A clinical photo of a skin lesion taken with a smartphone · skin type V · a female patient in their 50s: 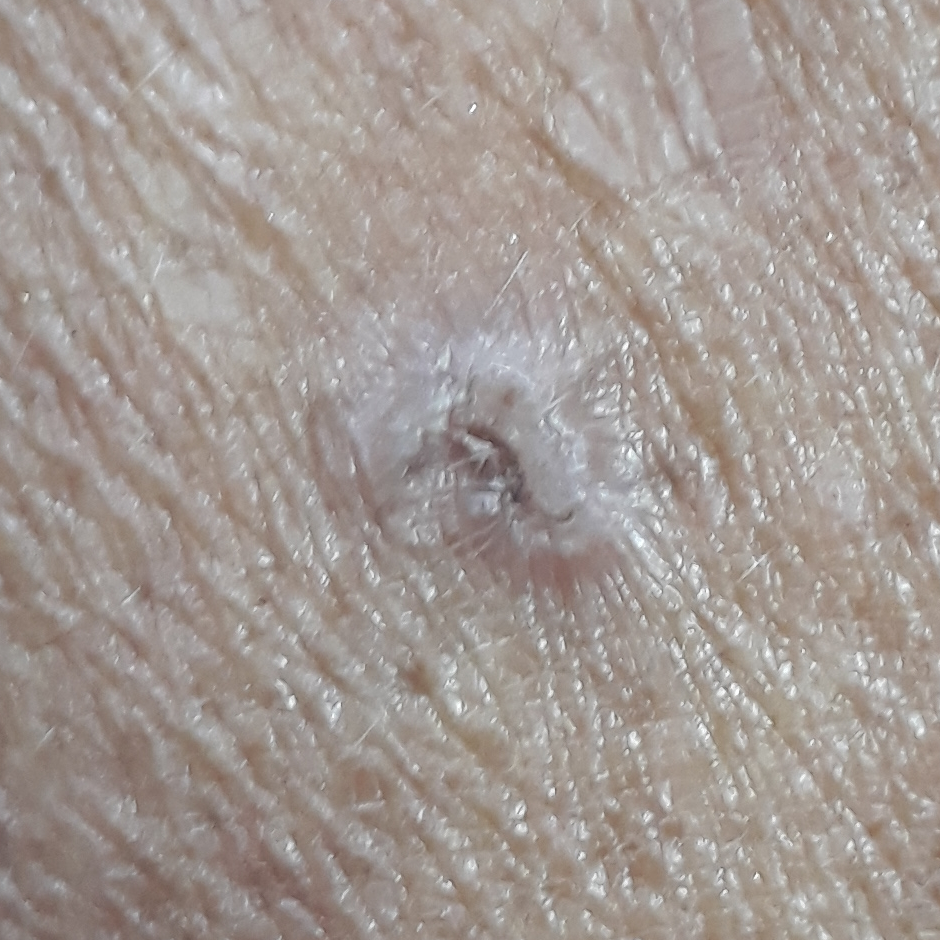Q: Where on the body is the lesion?
A: an arm
Q: Lesion size?
A: approx. 5 × 5 mm
Q: Any reported symptoms?
A: elevation, itching
Q: What is this lesion?
A: actinic keratosis (biopsy-proven)